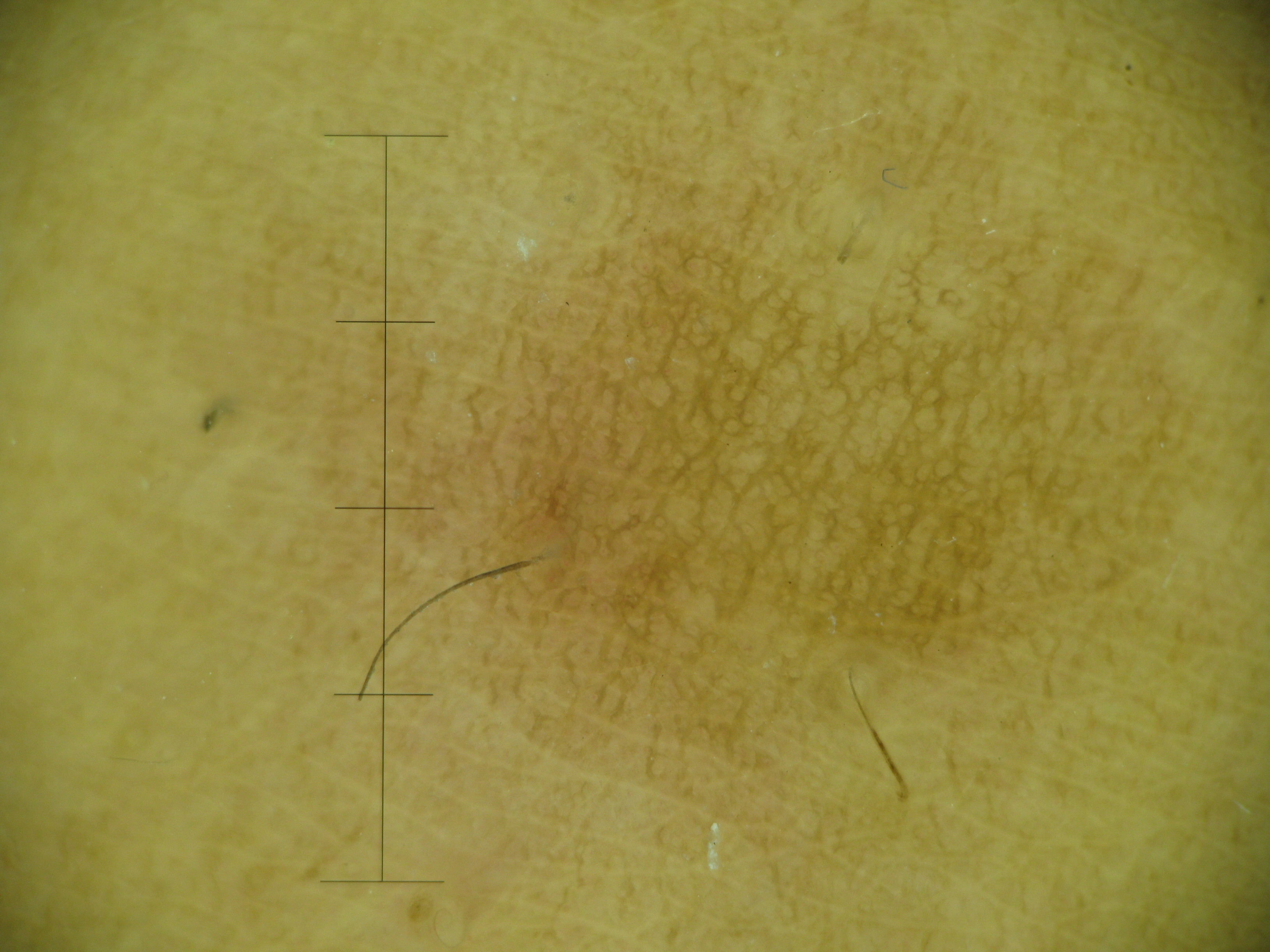Summary: A dermoscopic close-up of a skin lesion. The morphology is that of a fibro-histiocytic lesion. Conclusion: Labeled as a dermatofibroma.